A female subject 75 years of age. The patient says their skin tans without first burning. The patient describes having a moderate number of moles. Acquired for a research image collection, with no referral diagnosis.
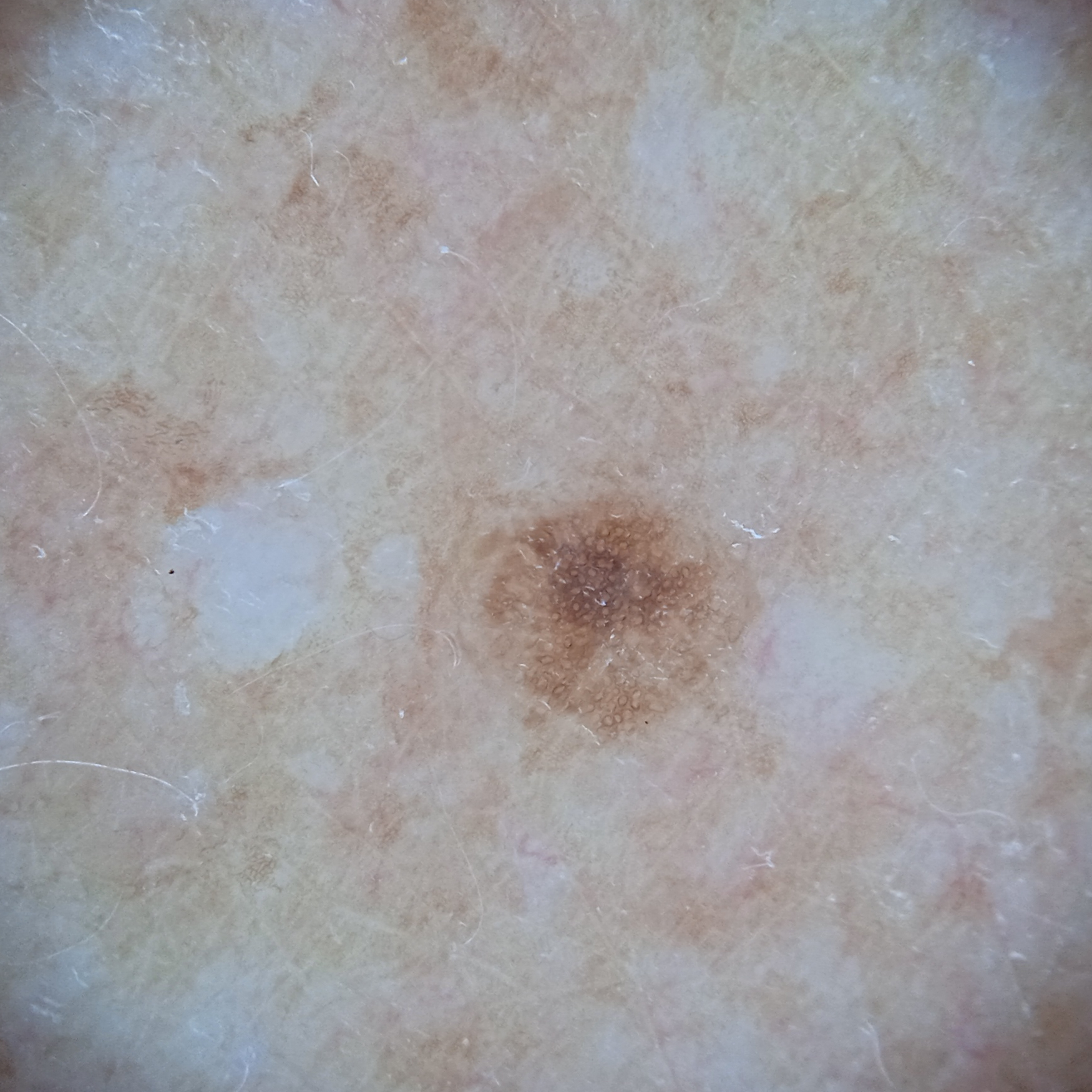The lesion measures approximately 2.7 mm. The lesion was assessed as a melanocytic nevus.